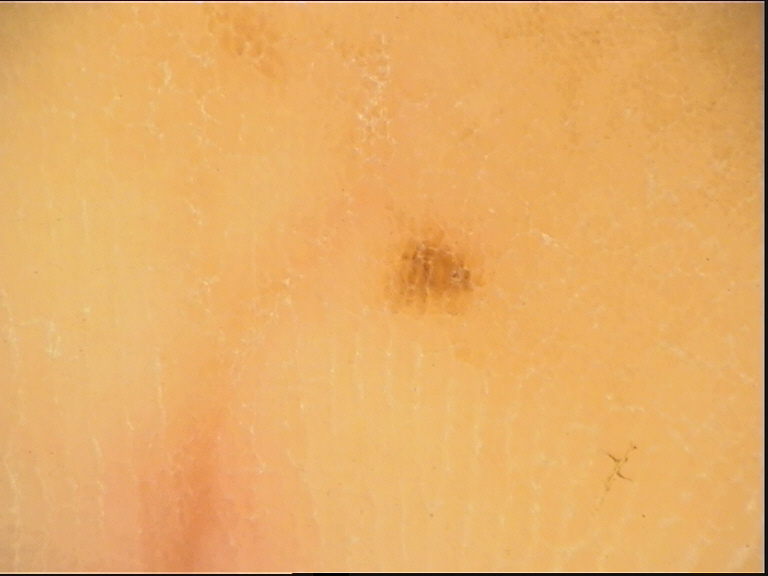Labeled as a banal lesion — an acral junctional nevus.